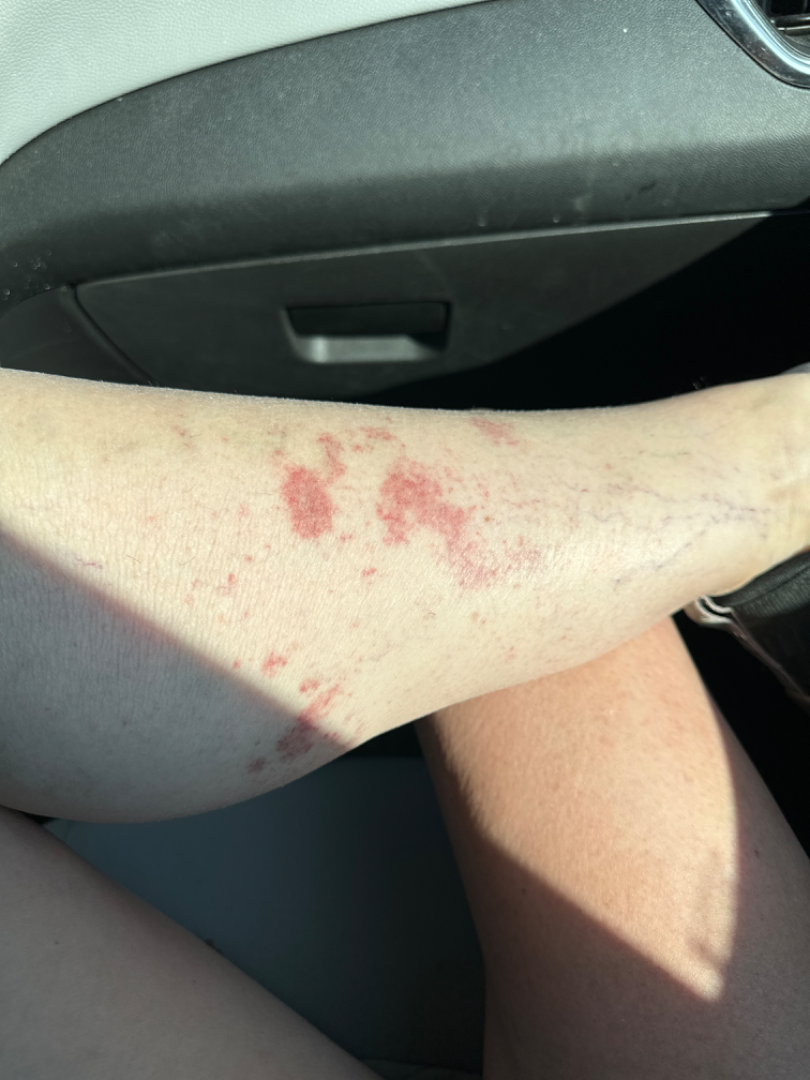Fitzpatrick III. The patient indicates associated fatigue. A close-up photograph. The affected area is the leg. The patient reported no relevant symptoms from the lesion. The condition has been present for about one day. The patient is a female aged 60–69. The leading consideration is Pigmented purpuric eruption; an alternative is Leukocytoclastic Vasculitis; less probable is Allergic Contact Dermatitis.